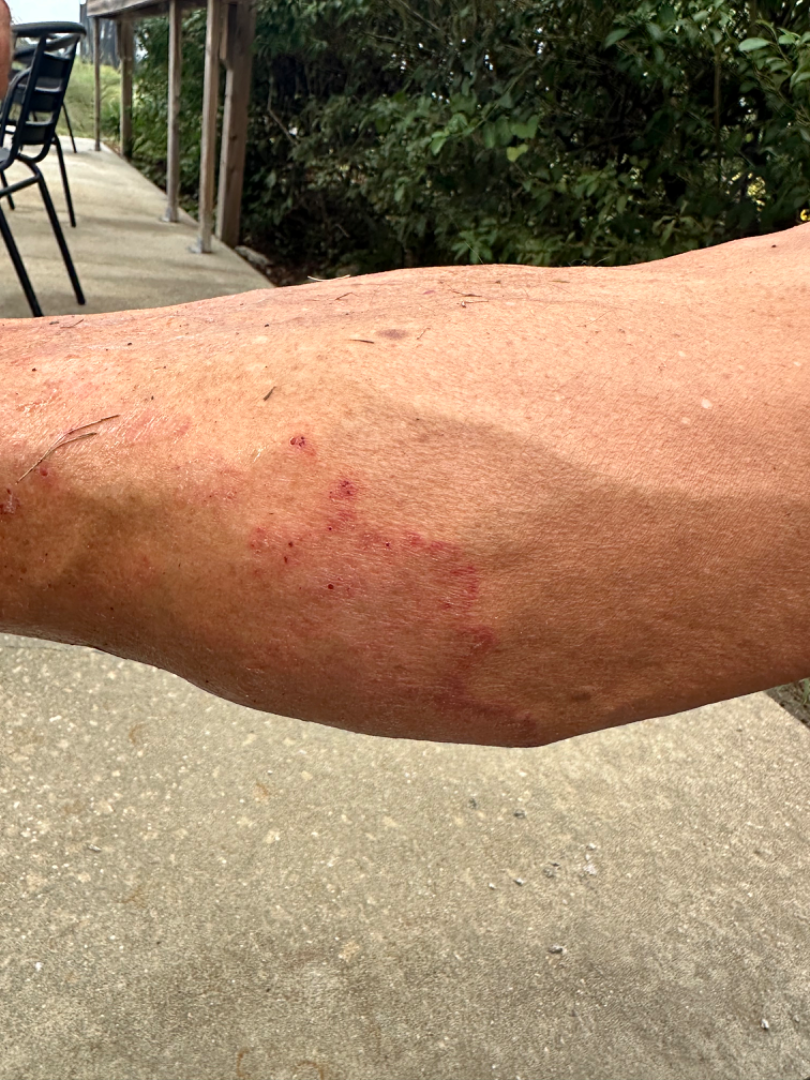A close-up photograph. On photographic review by a dermatologist, in keeping with Tinea.